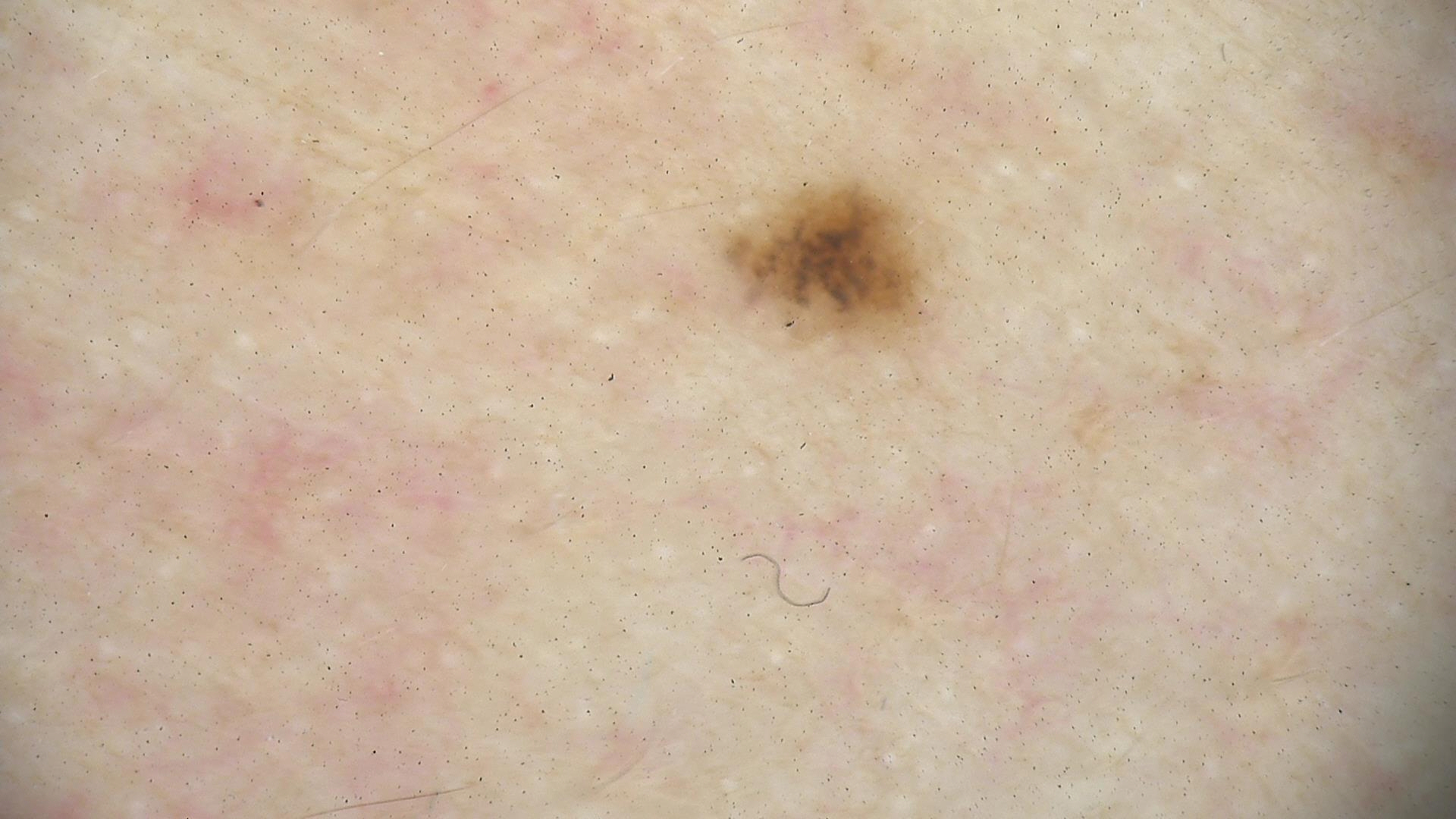image type: dermatoscopy
diagnosis: dysplastic junctional nevus (expert consensus)